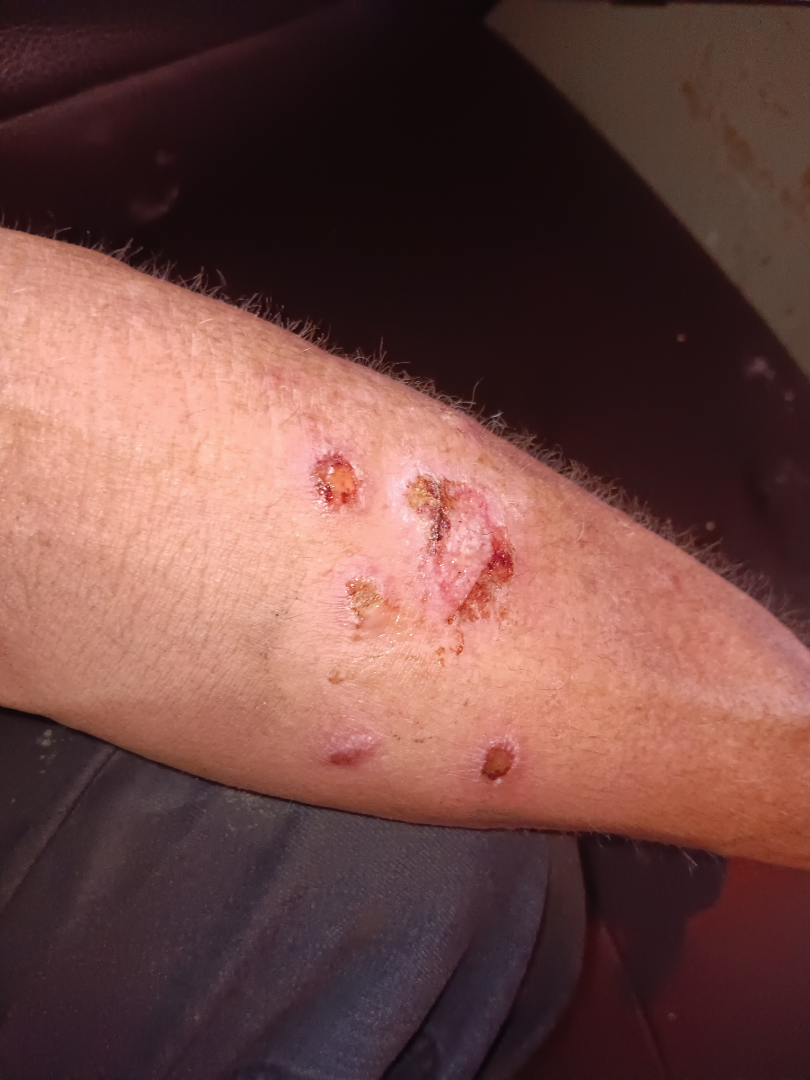| field | value |
|---|---|
| lesion texture | raised or bumpy, rough or flaky and fluid-filled |
| patient describes the issue as | a rash |
| affected area | head or neck, arm, leg and back of the hand |
| skin tone | Fitzpatrick phototype III |
| lesion symptoms | darkening, burning, bothersome appearance, enlargement, itching, bleeding and pain |
| framing | at a distance |
| symptom duration | more than one year |
| constitutional symptoms | fever, shortness of breath, fatigue, joint pain and chills |
| clinical impression | Abrasion, scrape, or scab and Ecthyma were considered with similar weight; also raised was Impetigo; less probable is Mycetoma |